A dermoscopic close-up of a skin lesion: 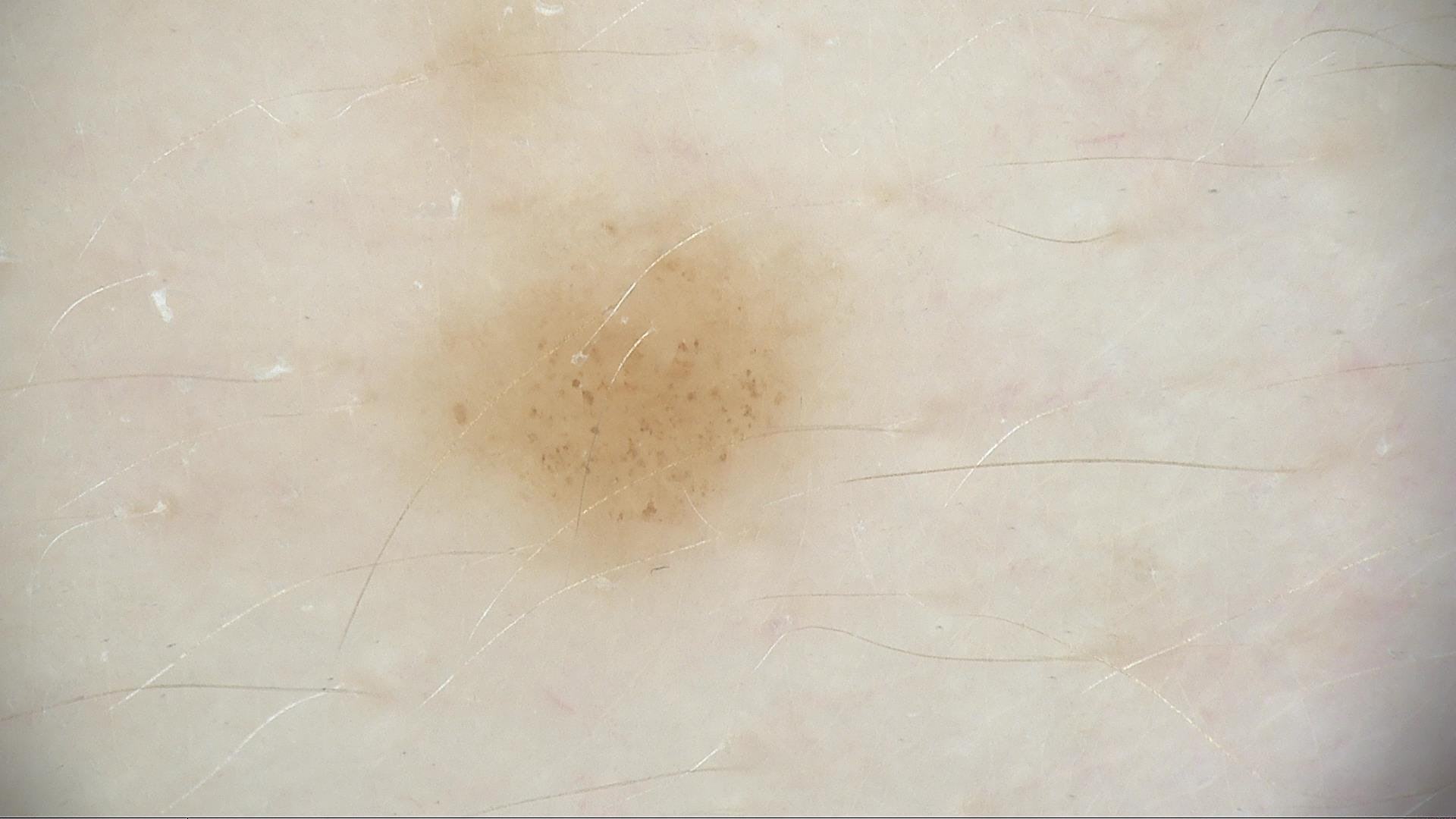* diagnostic label: dysplastic junctional nevus (expert consensus)